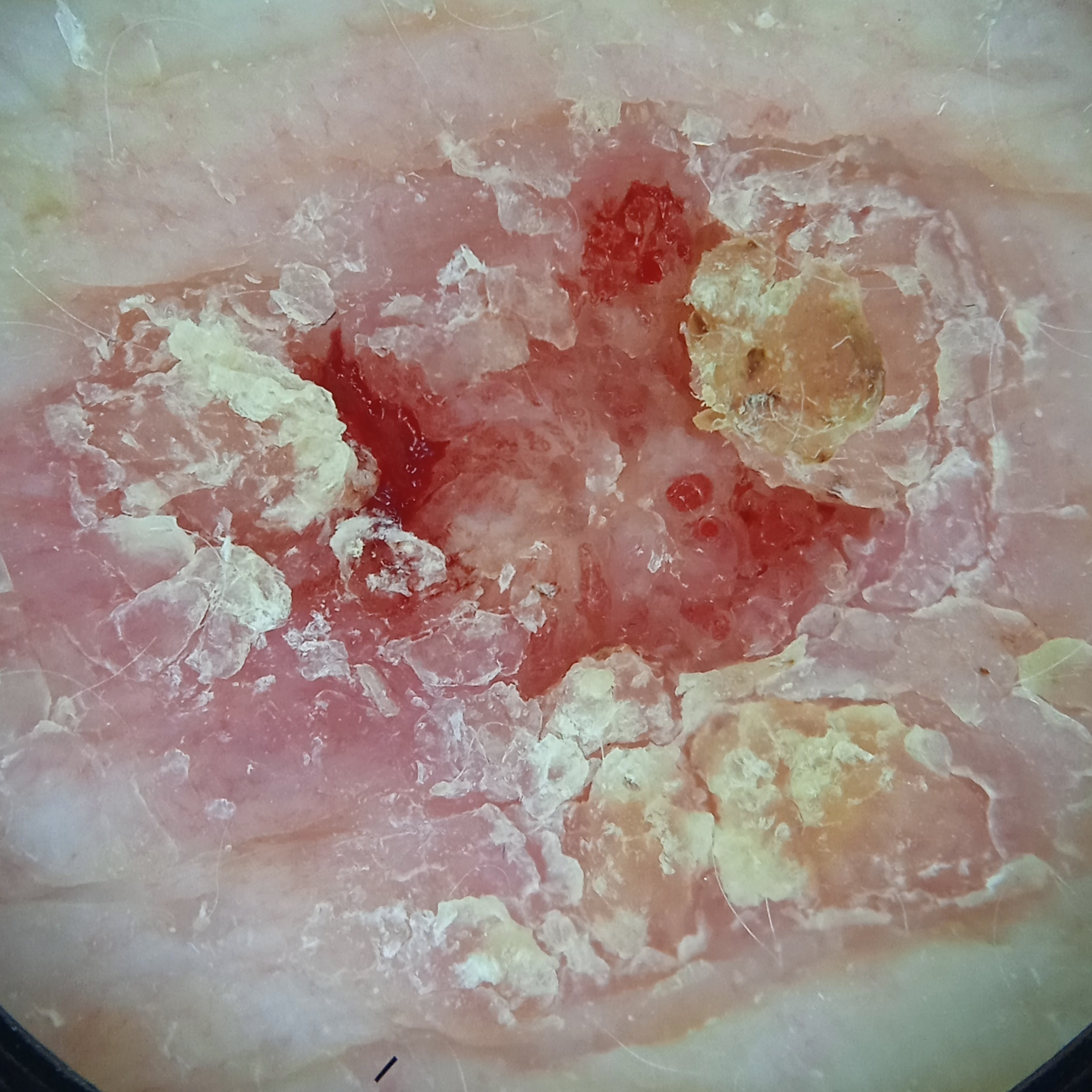The patient reports no immunosuppression. A dermoscopic image of a skin lesion. Referred for assessment of suspected Bowen's disease. A male subject aged 83. The lesion involves the torso. The lesion measures approximately 14.5 mm. The dermatologists' assessment was a squamous cell carcinoma.